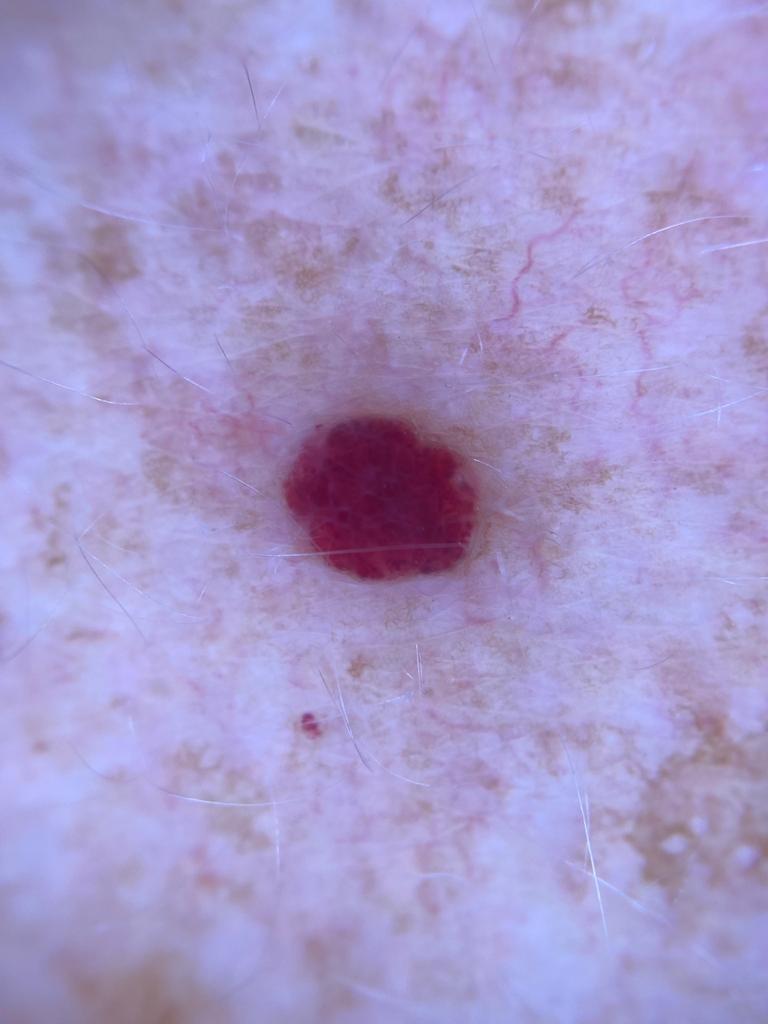The patient is Fitzpatrick skin type II. The lesion involves the trunk (the posterior trunk). Clinically diagnosed as a benign vascular lesion.